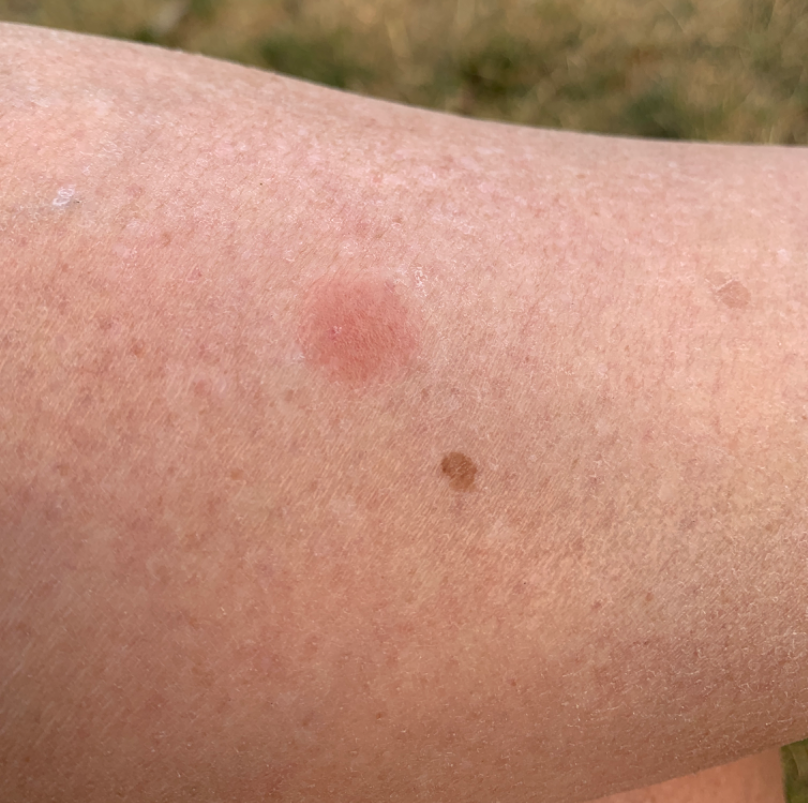The case was difficult to assess from the available photograph. Self-categorized by the patient as a growth or mole. The affected area is the leg. The patient indicates the condition has been present for one to four weeks. Texture is reported as rough or flaky and flat. Female patient, age 50–59. The photograph is a close-up of the affected area. The patient also reports joint pain and fatigue.